A dermatoscopic image of a skin lesion:
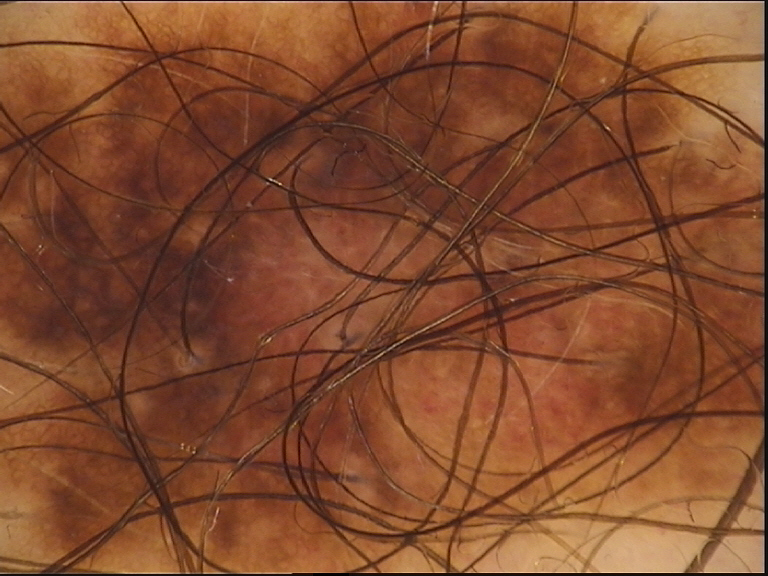– lesion type: banal
– assessment: compound nevus (expert consensus)